A contact-polarized dermoscopy image of a skin lesion. The patient was assessed as Fitzpatrick I. The chart notes a previous melanoma. A male subject aged around 60.
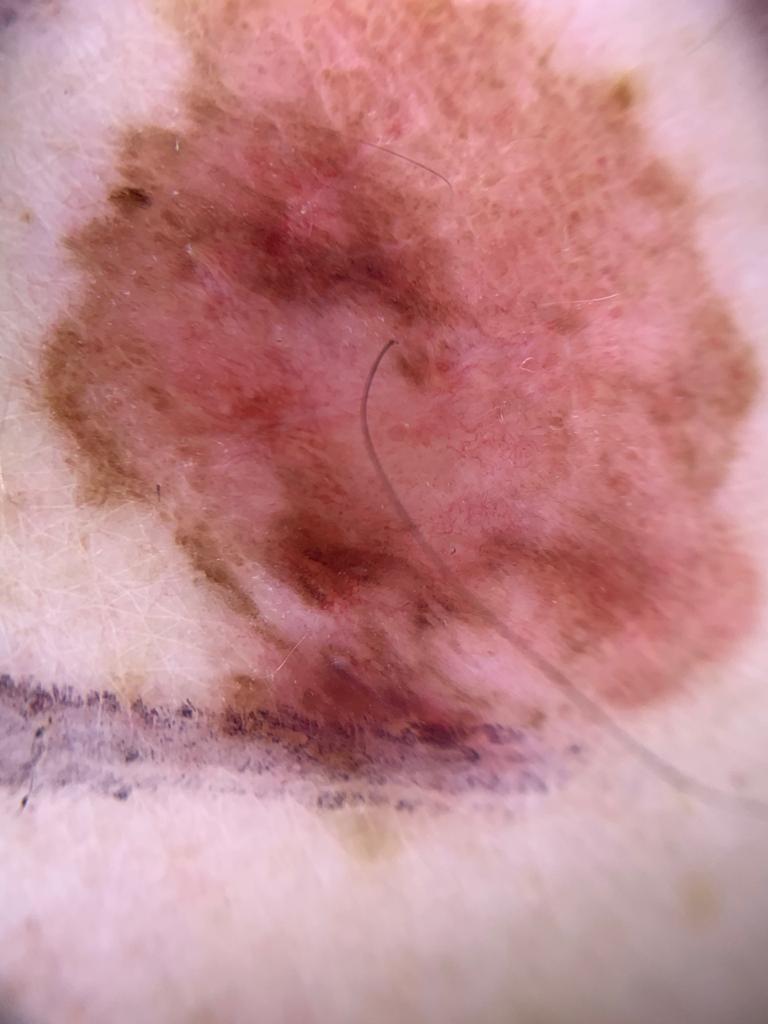  lesion_location:
    region: the trunk
    detail: the anterior trunk
  diagnosis:
    name: Melanoma
    malignancy: malignant
    confirmation: histopathology